Imaged for a research study, with no referral diagnosis recorded; few moles overall by the patient's own estimate; a male patient age 66; a skin lesion imaged with a dermatoscope; the patient says their skin reddens with sun exposure: 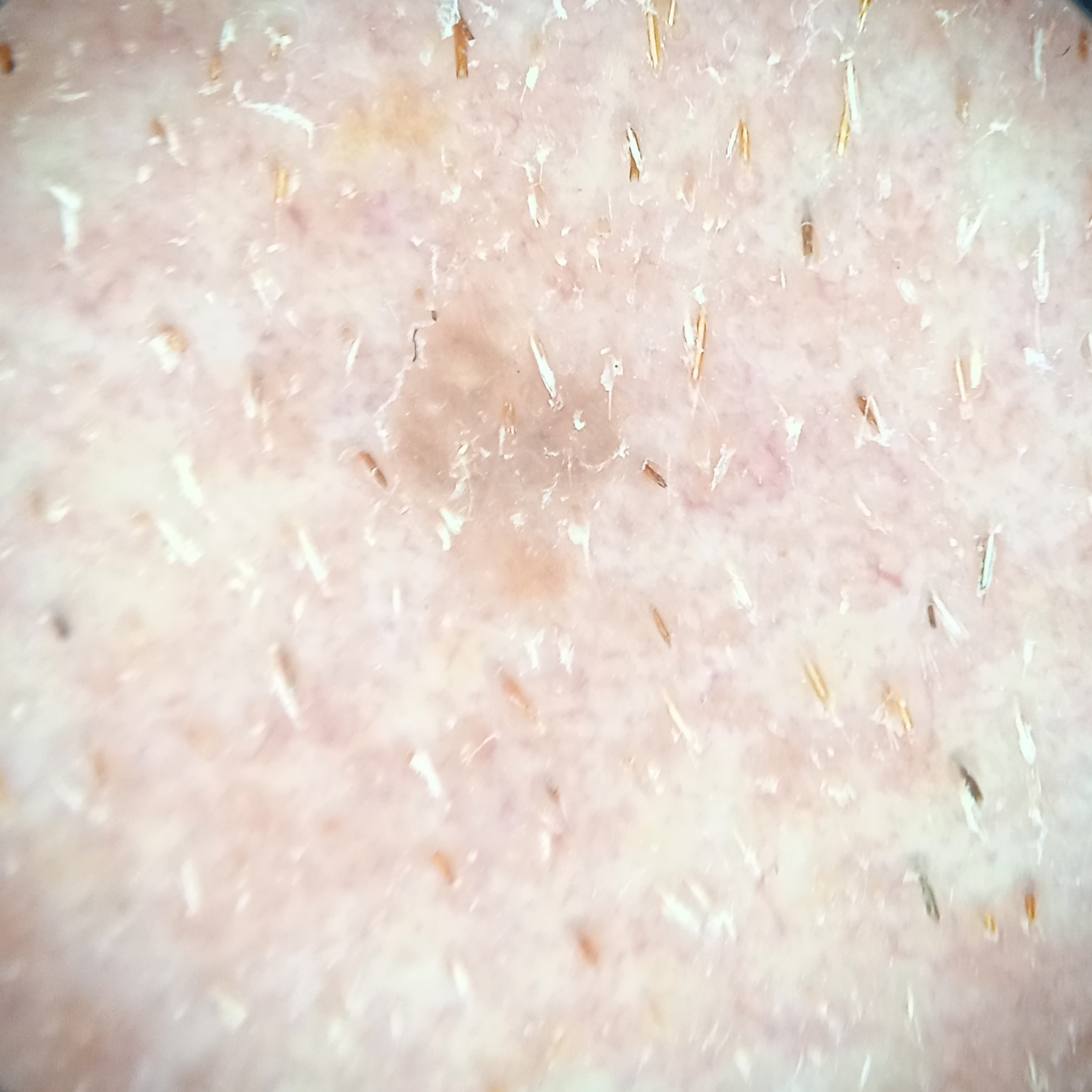body site: the face
diameter: 3 mm
assessment: seborrheic keratosis (dermatologist consensus)